A dermoscopic close-up of a skin lesion:
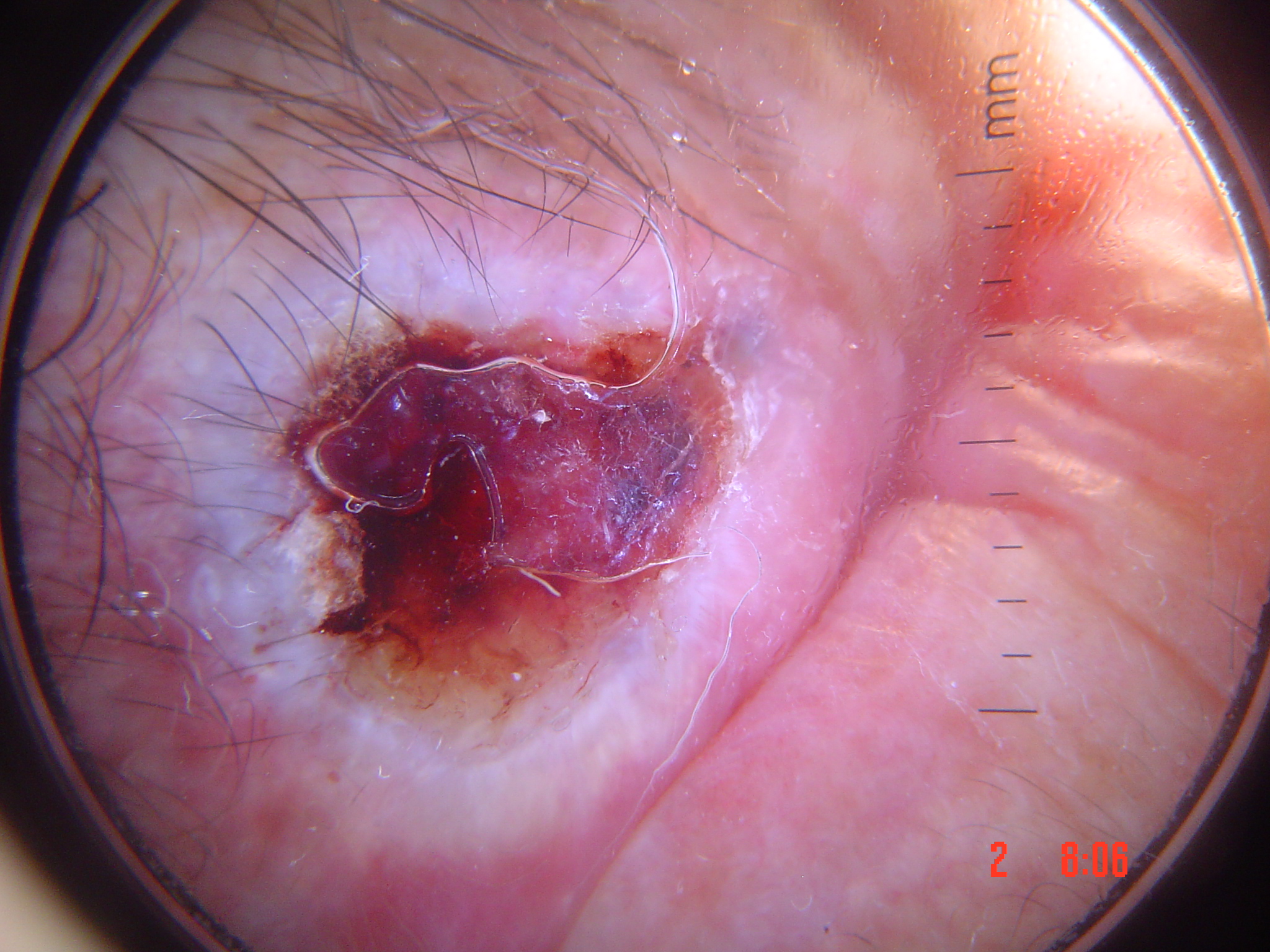Diagnosis: Histopathologically confirmed as a malignant lesion — a squamous cell carcinoma.